A skin lesion imaged with a dermatoscope.
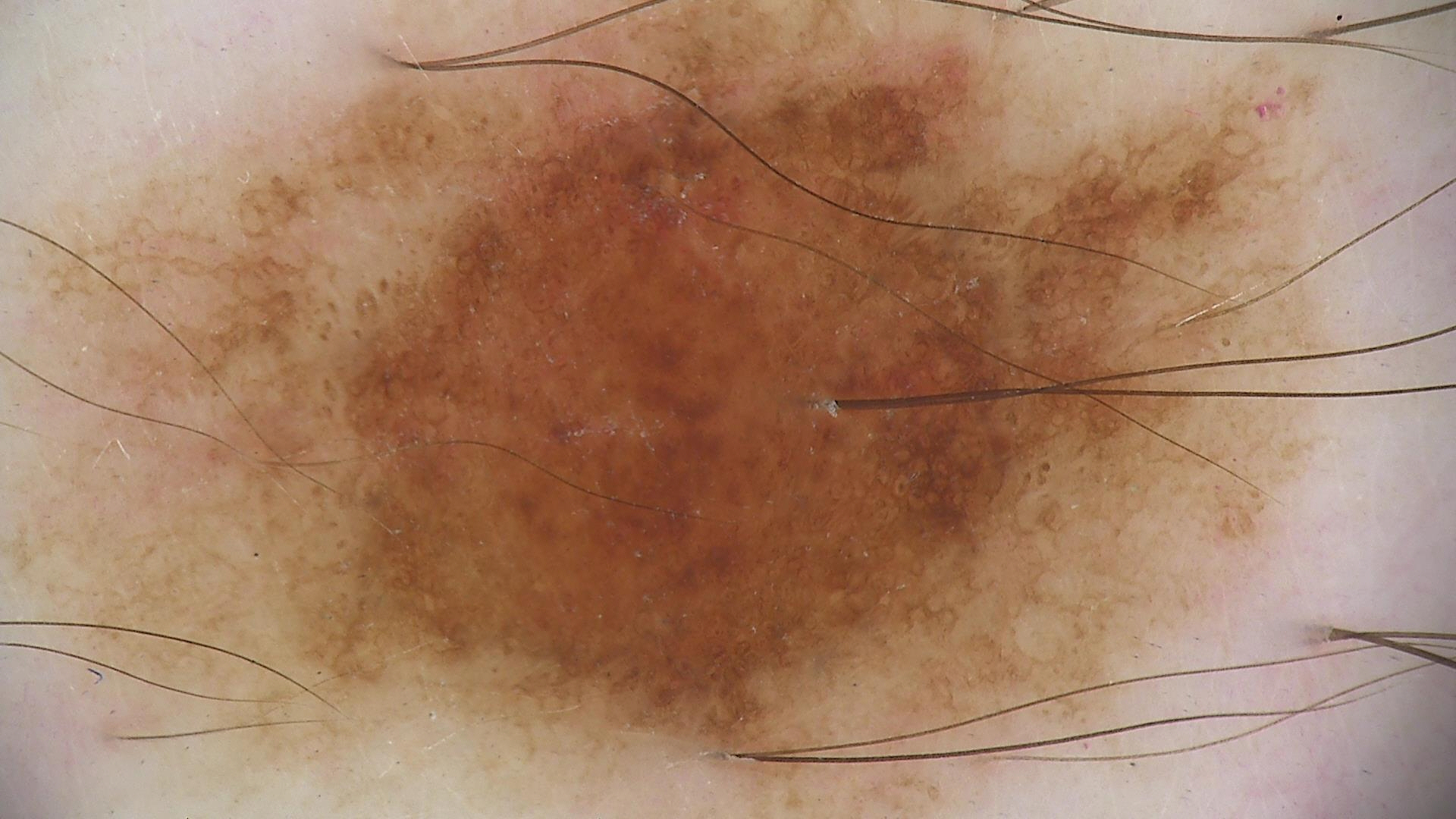label: dysplastic compound nevus (expert consensus).